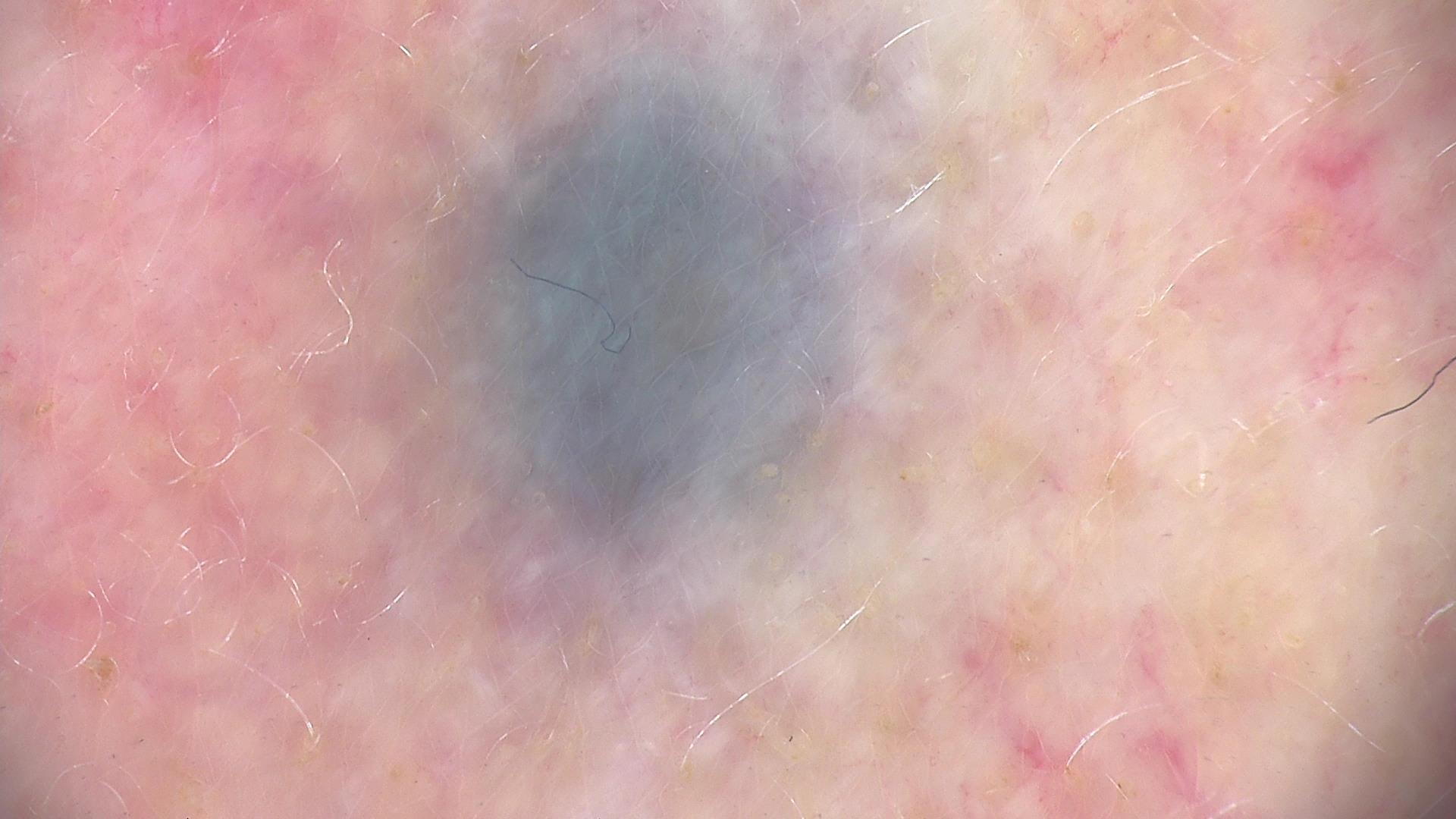| field | value |
|---|---|
| image | dermatoscopy |
| label | blue nevus (expert consensus) |